A dermatoscopic image of a skin lesion:
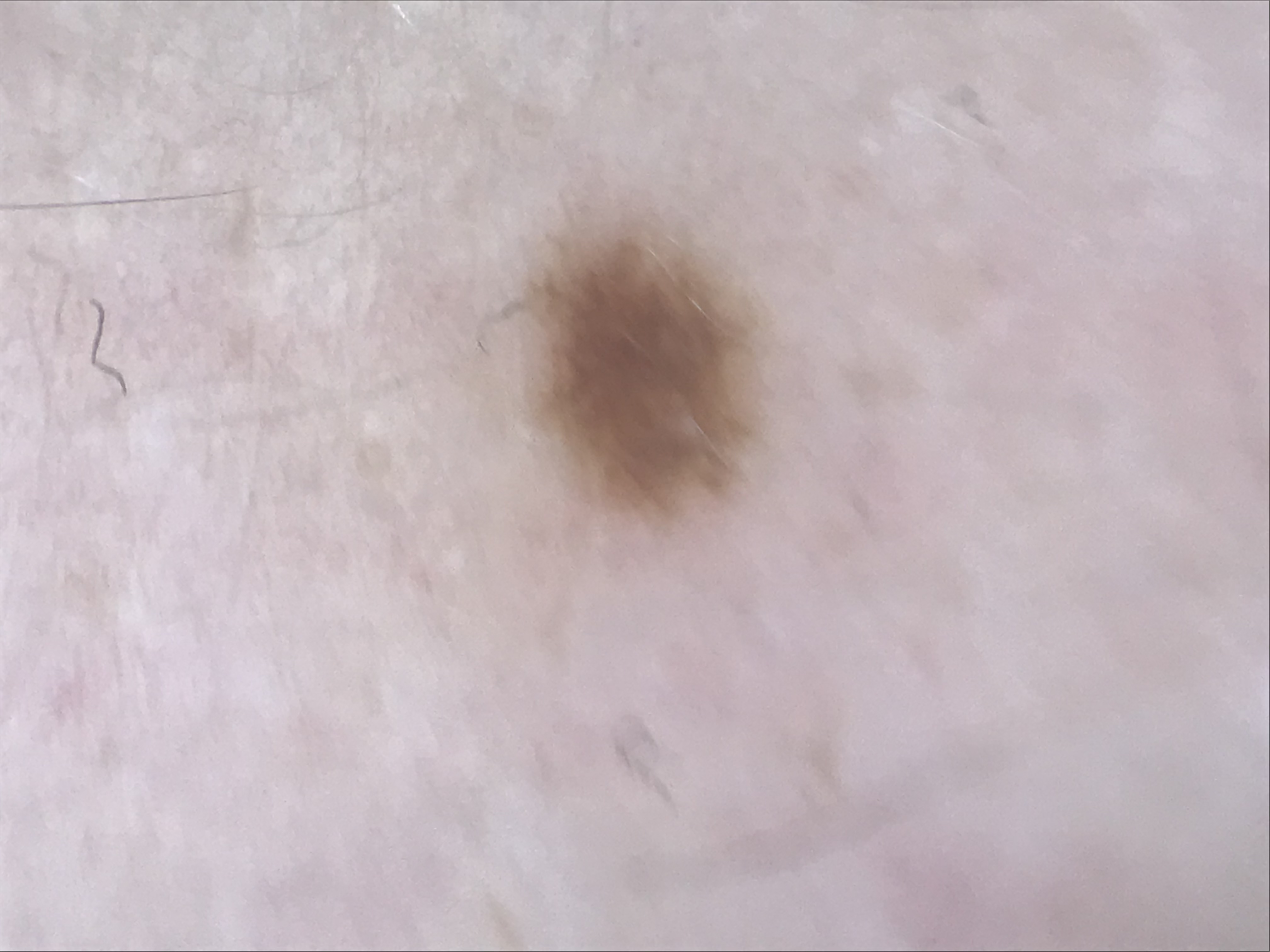label: junctional nevus (expert consensus).